Self-categorized by the patient as a rash · the contributor is a female aged 30–39 · the contributor notes the lesion is flat · the affected area is the leg · the patient reported no relevant symptoms from the lesion · this image was taken at an angle · the condition has been present for more than five years:
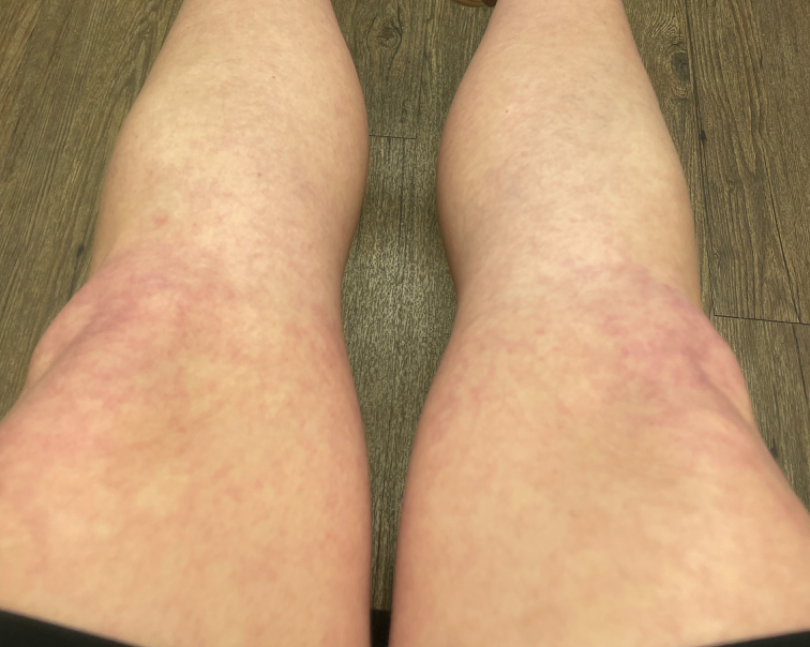Case summary:
– differential — three independent reviewers: the favored diagnosis is Livedo reticularis; an alternative is Erythema ab igne